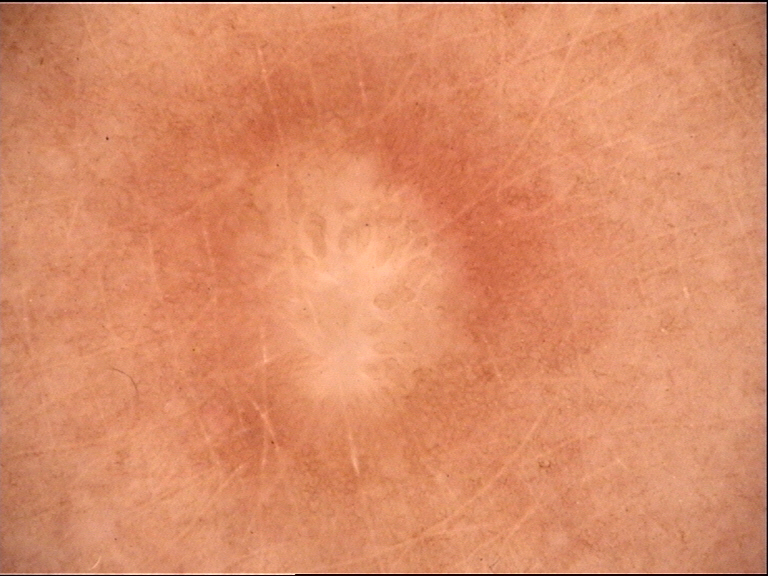<case>
<image>dermatoscopy</image>
<lesion_type>
<main_class>fibro-histiocytic</main_class>
</lesion_type>
<diagnosis>
<name>dermatofibroma</name>
<code>df</code>
<malignancy>benign</malignancy>
<super_class>non-melanocytic</super_class>
<confirmation>expert consensus</confirmation>
</diagnosis>
</case>